A dermoscopy image of a single skin lesion.
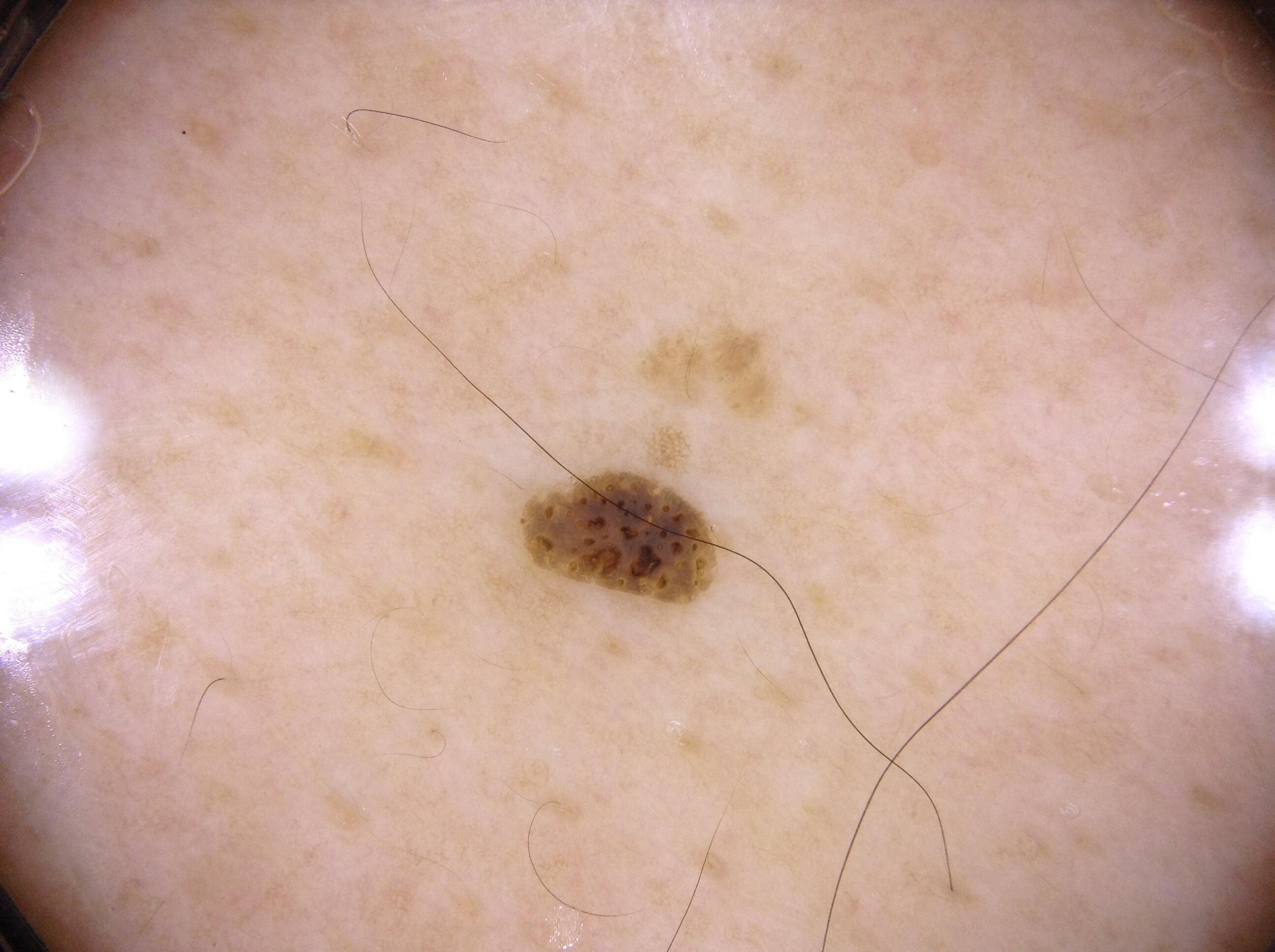<dermoscopy>
<dermoscopic_features>
  <present/>
  <absent>pigment network, negative network, streaks, milia-like cysts</absent>
</dermoscopic_features>
<lesion_location>
  <bbox_xyxy>512, 466, 726, 612</bbox_xyxy>
</lesion_location>
<lesion_extent>small</lesion_extent>
<diagnosis>
  <name>seborrheic keratosis</name>
  <malignancy>benign</malignancy>
  <lineage>keratinocytic</lineage>
  <provenance>clinical</provenance>
</diagnosis>
</dermoscopy>